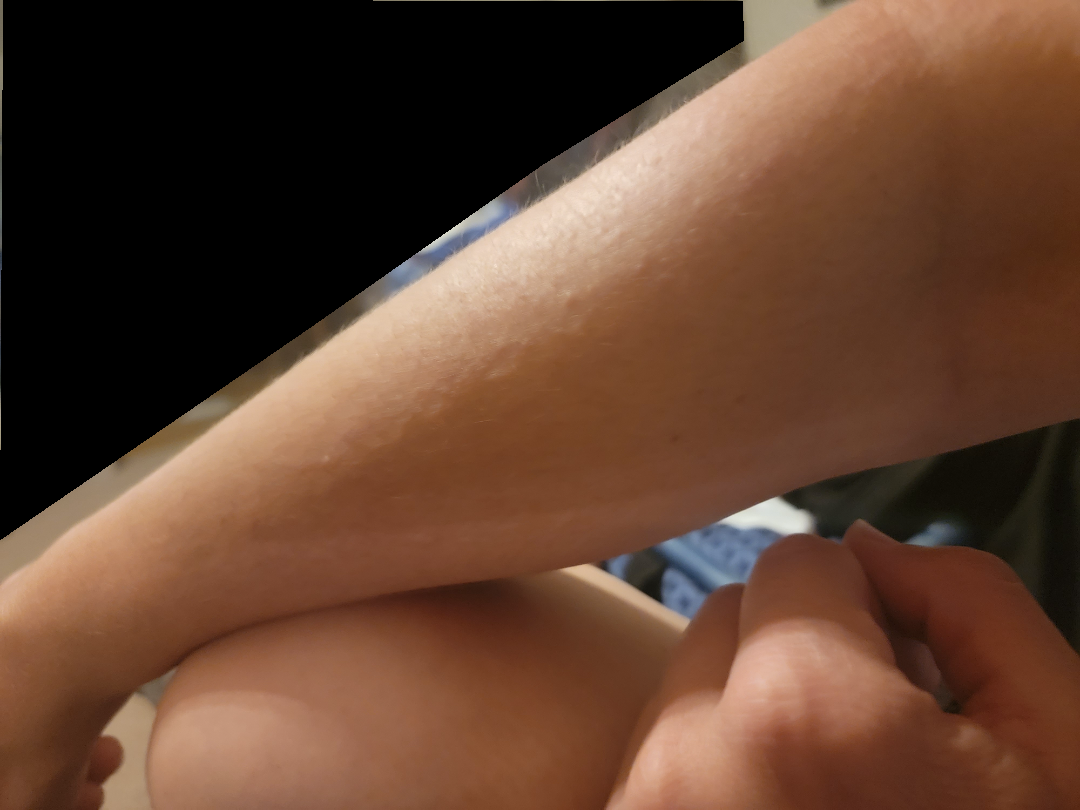Q: What was the assessment?
A: could not be assessed
Q: Patient's own categorization?
A: a rash
Q: Fitzpatrick or Monk tone?
A: self-reported Fitzpatrick skin type III
Q: Image view?
A: close-up
Q: Patient demographics?
A: female, age 40–49
Q: What is the lesion texture?
A: raised or bumpy
Q: Reported symptoms?
A: itching and burning
Q: How long has this been present?
A: less than one week
Q: What is the affected area?
A: leg and arm
Q: Any systemic symptoms?
A: none reported